The affected area is the back of the torso, sole of the foot, head or neck, palm and top or side of the foot. This is a close-up image — 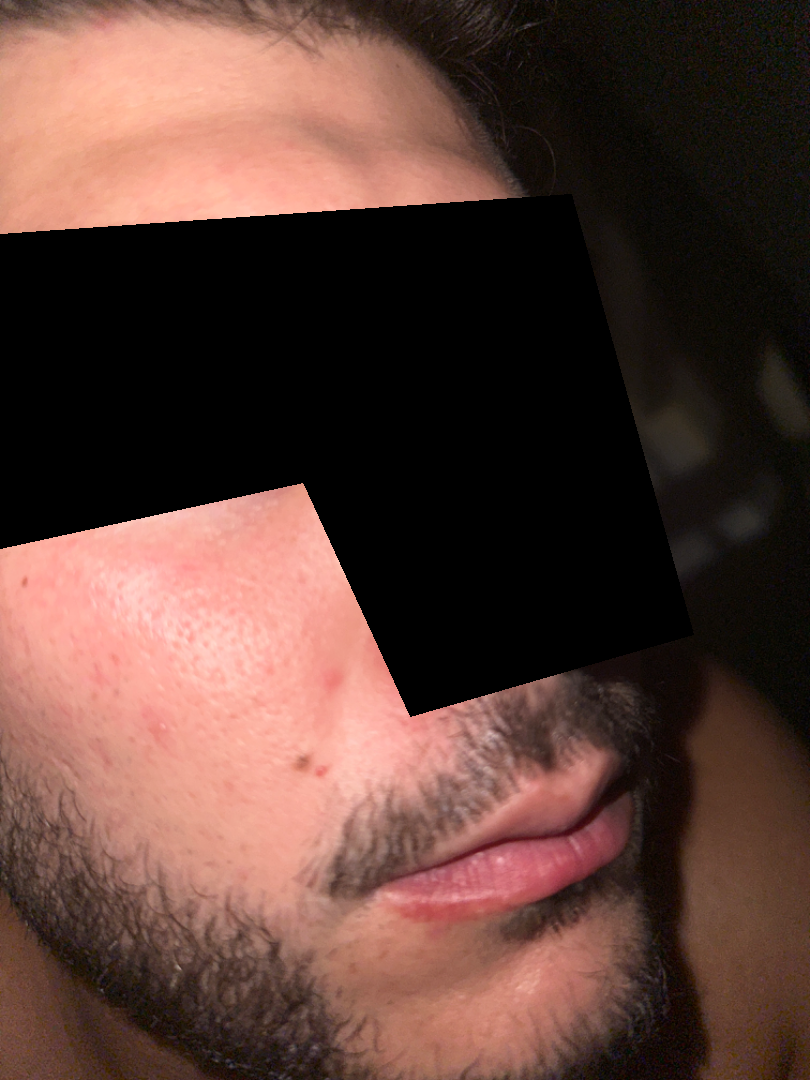The condition has been present for less than one week. Skin tone: Fitzpatrick phototype III; lay graders estimated Monk skin tone scale 2–3. The contributor reports bothersome appearance. Self-categorized by the patient as a rash. A single dermatologist reviewed the case: the favored diagnosis is Acne; also on the differential is Rosacea.